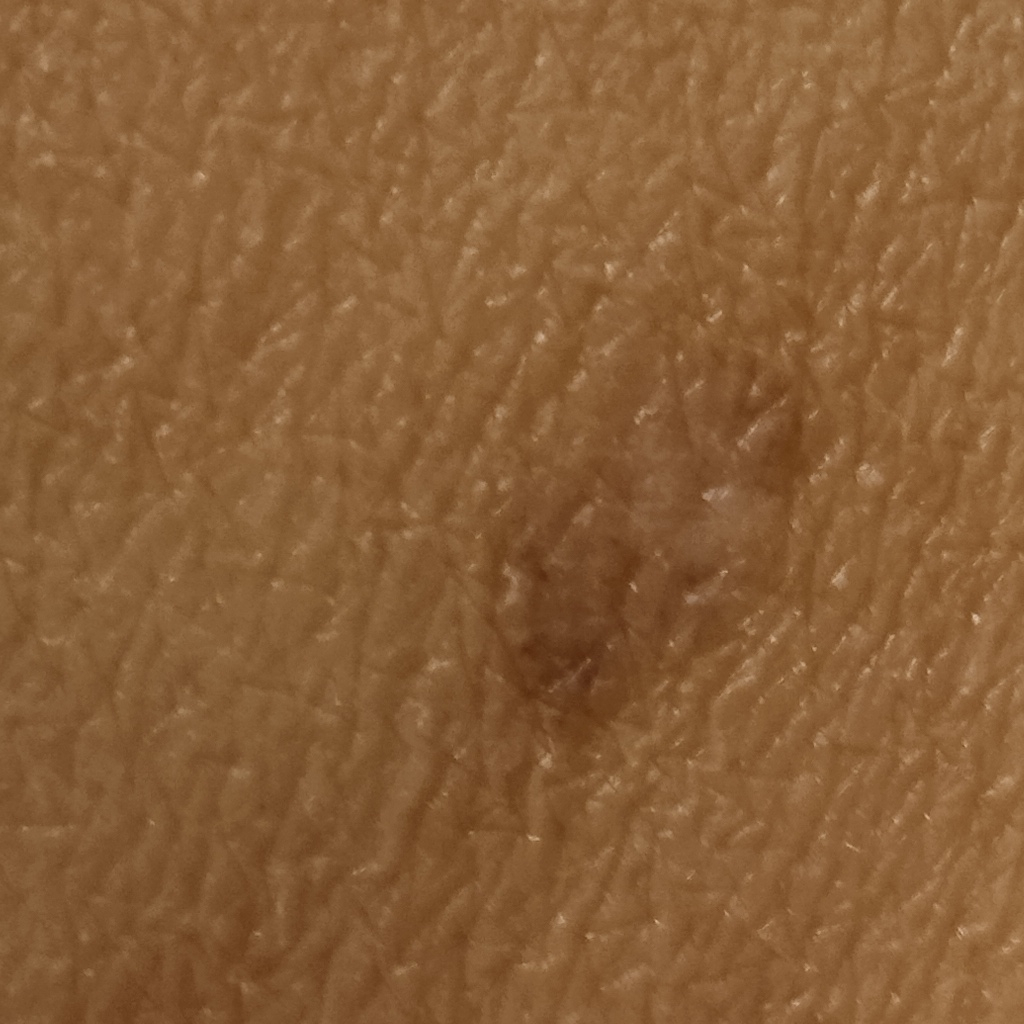mole_burden: few melanocytic nevi overall
image: clinical photo
sun_reaction: skin tans without first burning
patient:
  age: 60
  sex: female
risk_factors:
  positive:
    - a personal history of cancer
    - a personal history of skin cancer
  negative:
    - no immunosuppression
    - no prior organ transplant
lesion_location: the torso
lesion_size:
  diameter_mm: 3.4
diagnosis:
  name: melanocytic nevus
  malignancy: benign